A male patient 67 years of age. On a questionnaire the patient reported a personal history of skin cancer. Few moles overall by the patient's own estimate. A dermatoscopic image of a skin lesion — 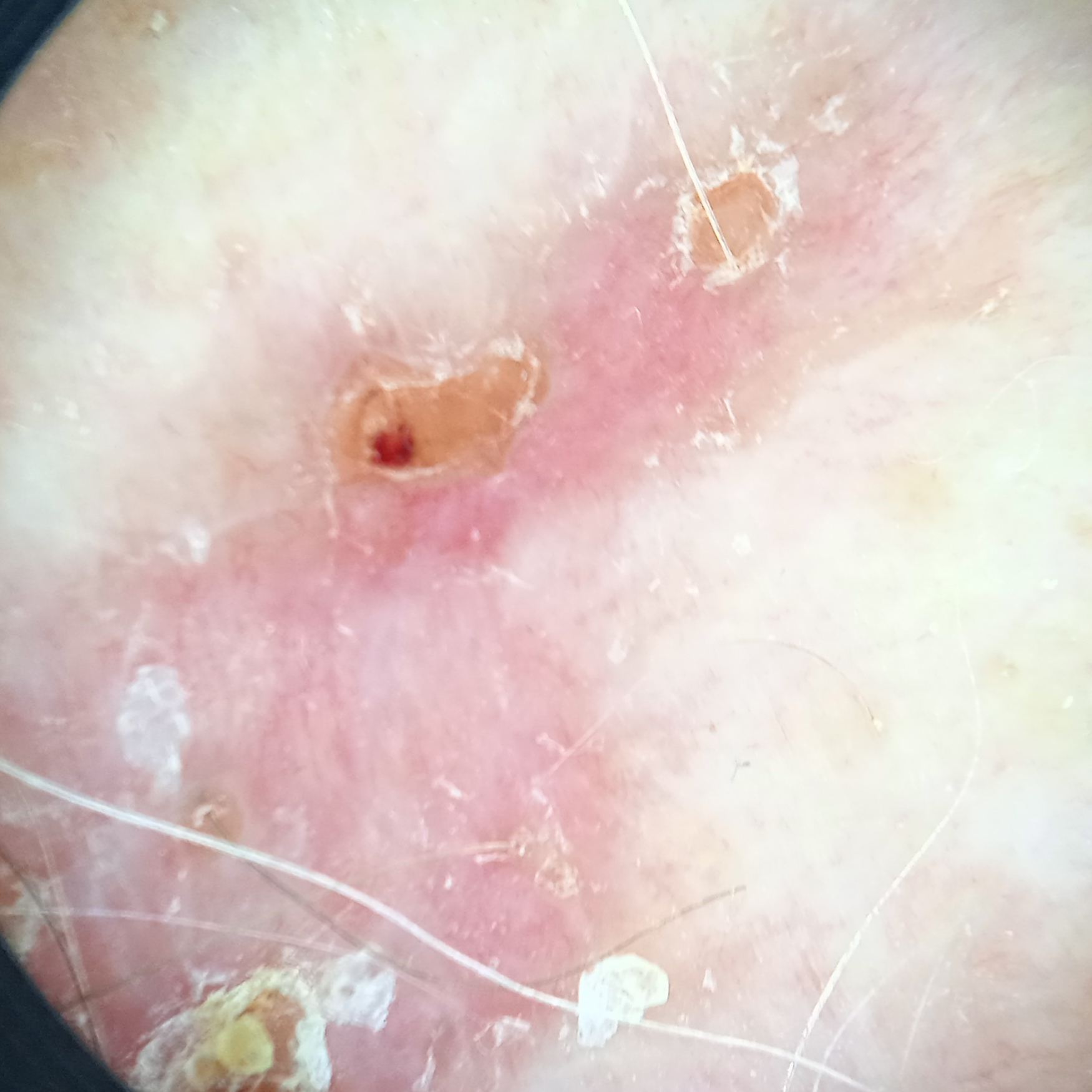<record>
<diagnosis>
<name>basal cell carcinoma</name>
<malignancy>malignant</malignancy>
<procedure>punch biopsy</procedure>
<tumor_thickness_mm>0.8</tumor_thickness_mm>
</diagnosis>
</record>